The patient is a male aged approximately 80. A dermoscopic close-up of a skin lesion.
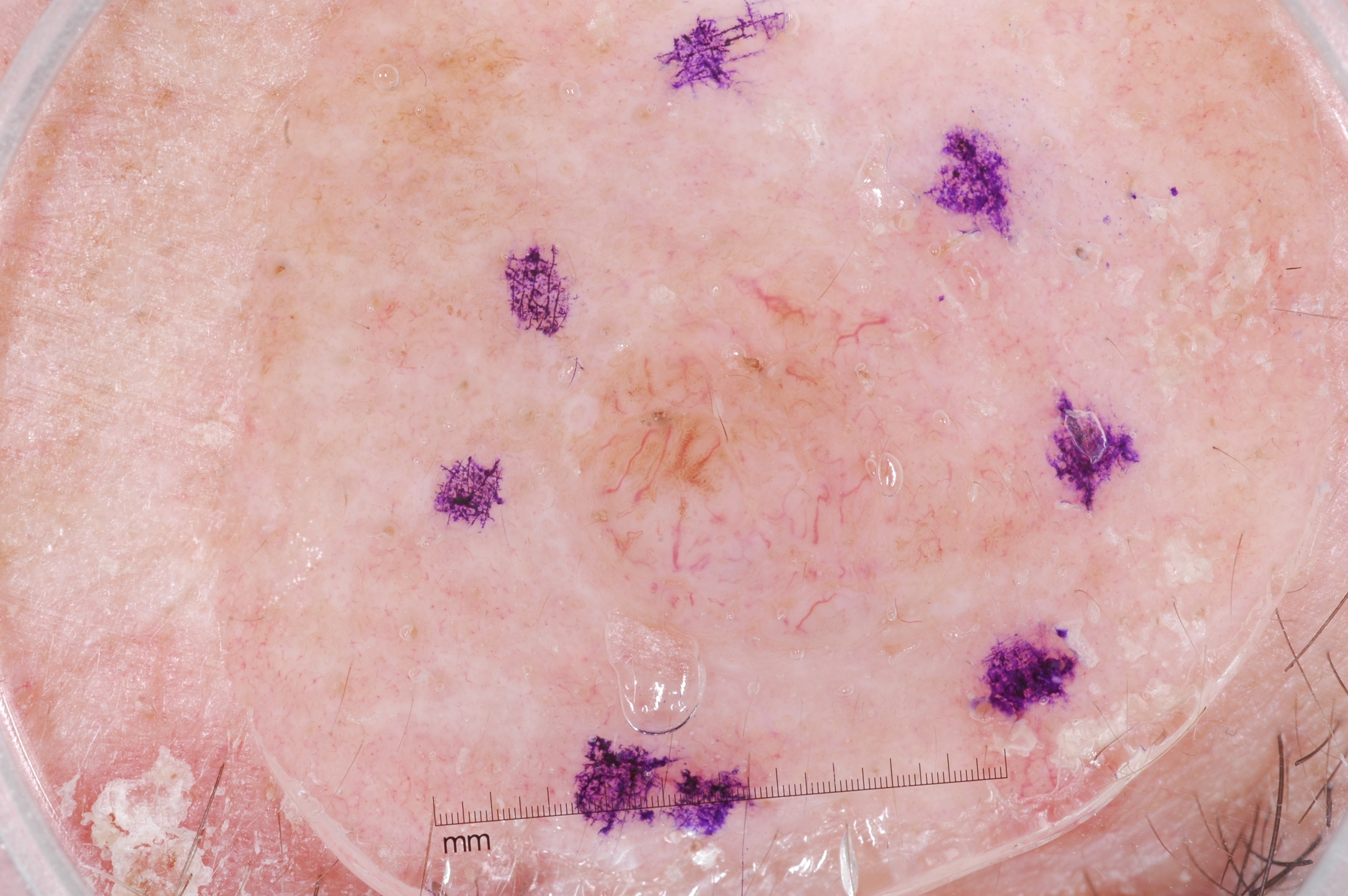dermoscopic features not present = negative network, pigment network, streaks, and milia-like cysts; extent = moderate; bounding box = [530,257,1049,657]; diagnosis = a melanocytic nevus.